A dermatoscopic image of a skin lesion: 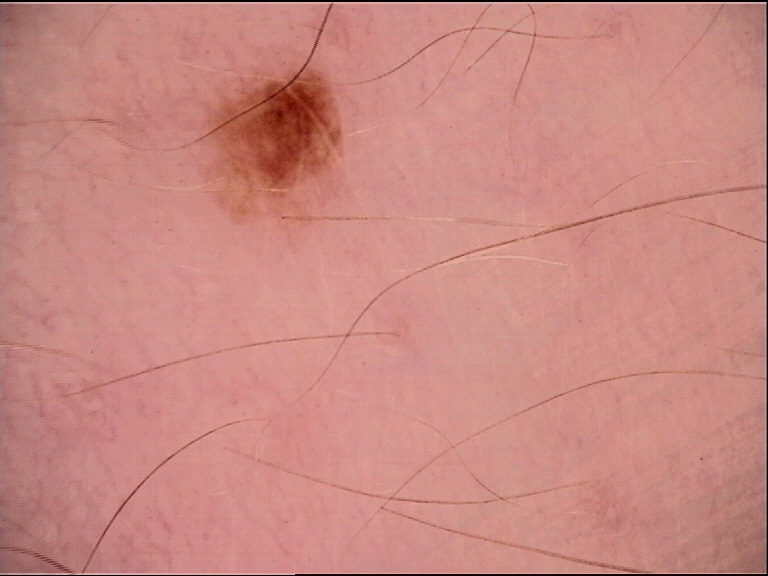Diagnosed as a benign lesion — a dysplastic junctional nevus.